Fitzpatrick II. A female subject age 32. A clinical photograph showing a skin lesion. The chart records pesticide exposure and no prior malignancy (patient or family):
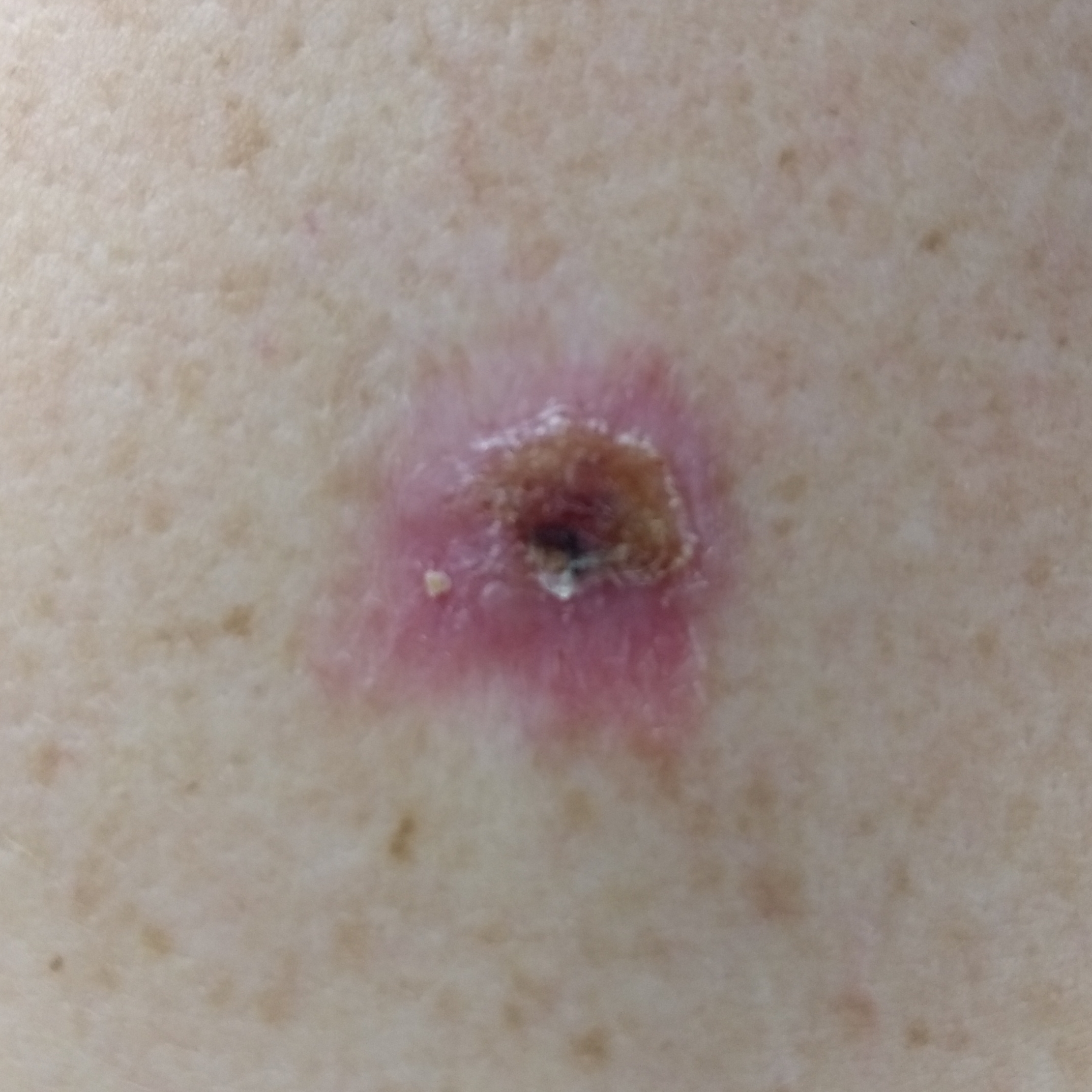Summary: The lesion involves the back. Measuring about 13 × 12 mm. The patient describes that the lesion has bled, is elevated, and itches, but has not grown. Diagnosis: Confirmed on histopathology as a basal cell carcinoma.